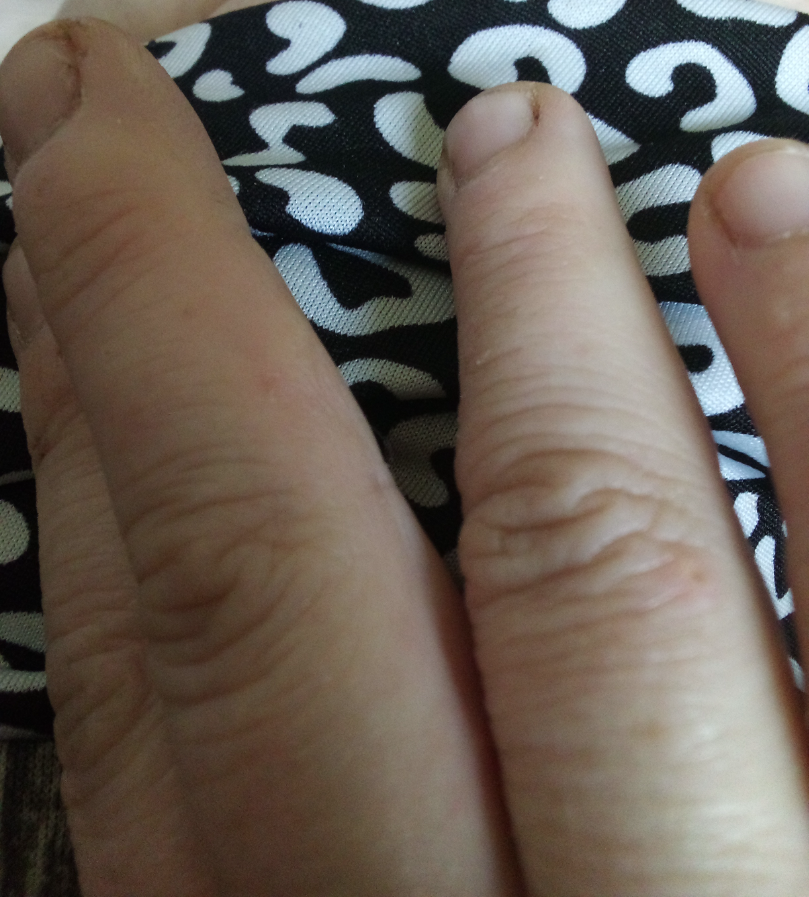| field | value |
|---|---|
| skin tone | Fitzpatrick II; lay graders estimated Monk Skin Tone 1 (US pool) or 2 (India pool) |
| contributor | female, age 40–49 |
| lesion texture | fluid-filled and raised or bumpy |
| patient describes the issue as | a rash |
| framing | at an angle |
| constitutional symptoms | chills |
| reported symptoms | itching and burning |
| present for | less than one week |
| assessment | the favored diagnosis is Eczema; also raised was Scabies |